The affected area is the arm · the photograph was taken at an angle · the patient reports itching:
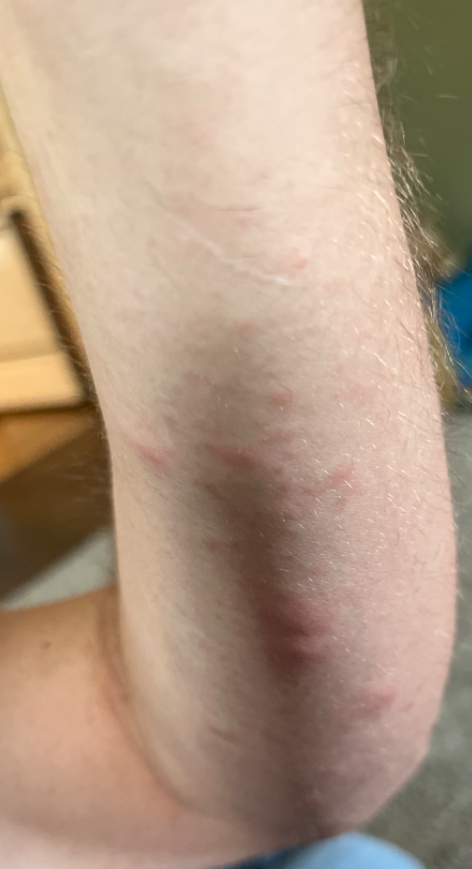Q: What is the differential diagnosis?
A: the leading impression is Urticaria; with consideration of Insect Bite